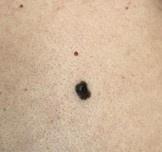An overview clinical photograph of a skin lesion.
A male subject aged 38-42.
The patient was assessed as skin type II.
The lesion involves the posterior trunk.
Histopathological examination showed a melanoma.